A dermoscopic image of a skin lesion: 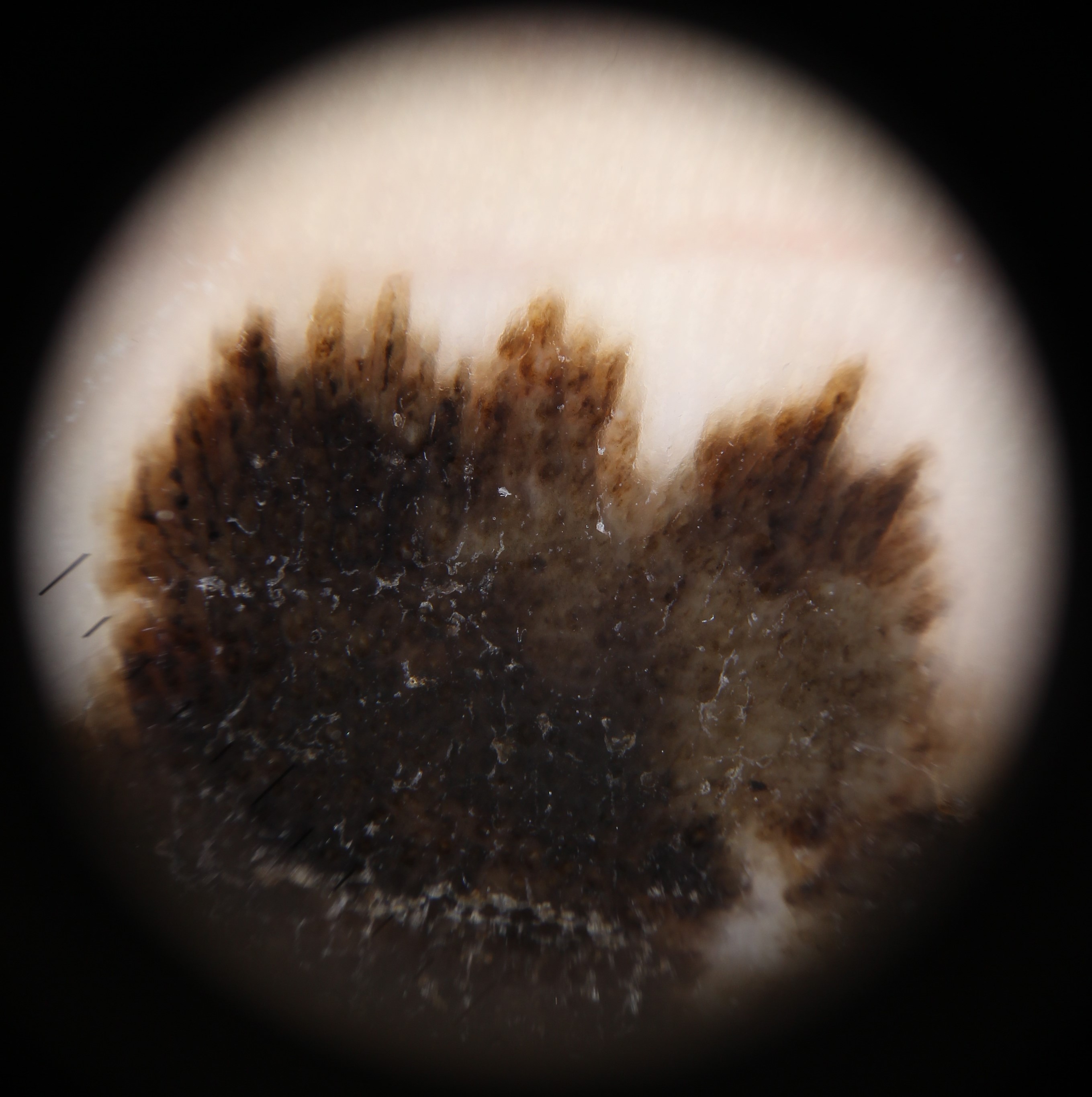The biopsy diagnosis was a skin cancer — an acral lentiginous melanoma.